Recorded as Fitzpatrick II; a male patient aged approximately 85 or older; the chart documents a previous melanoma — 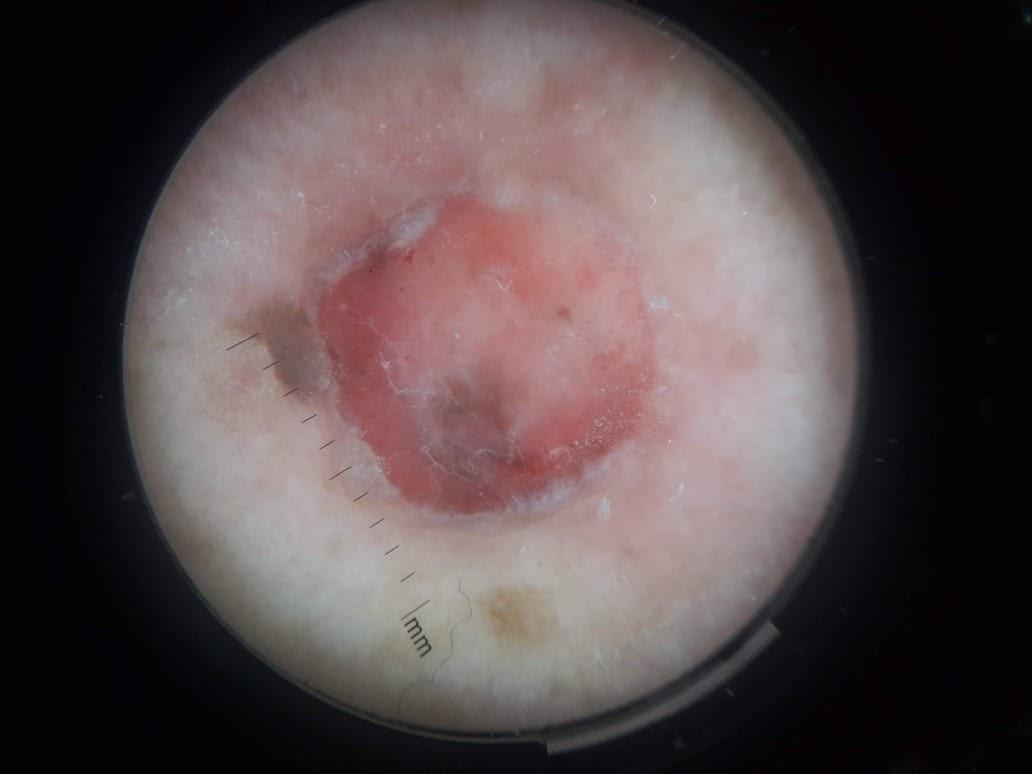site: the trunk (the posterior trunk)
diagnosis: Melanoma (biopsy-proven)